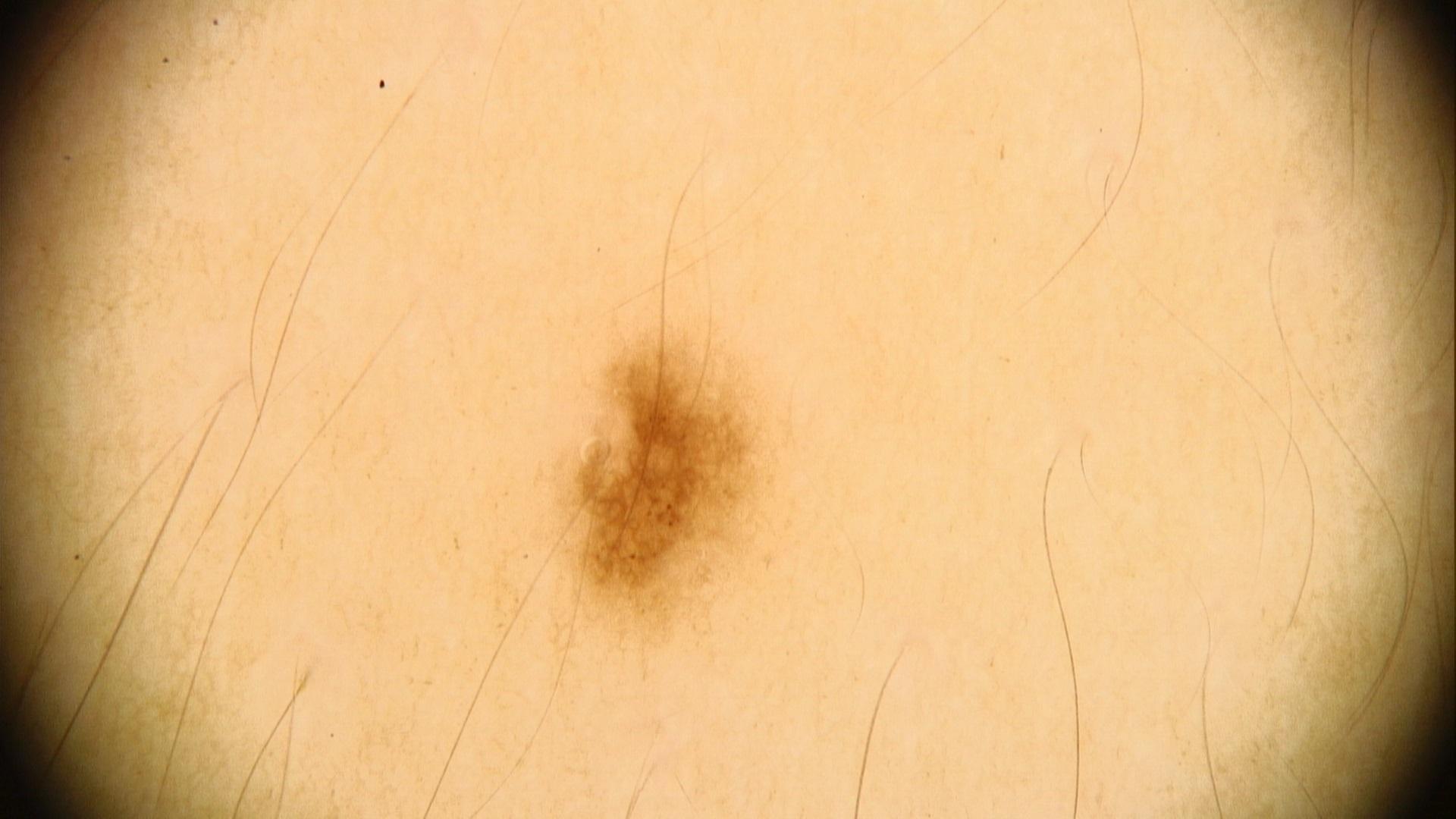Findings:
– location · the trunk
– assessment · Nevus